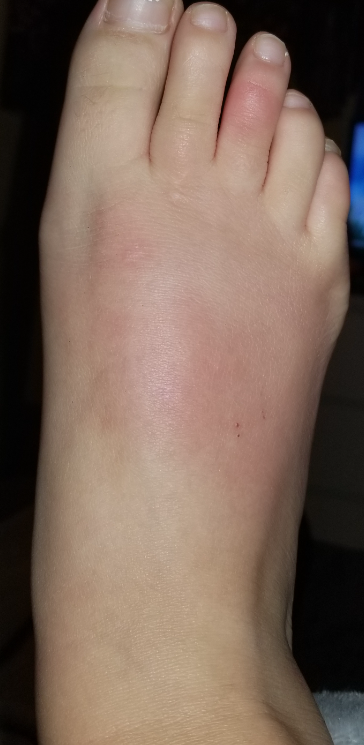Three dermatologists each reviewed the case: most likely Urticaria; possibly Superficial frostbite; also raised was Insect Bite; a remote consideration is Eczema.